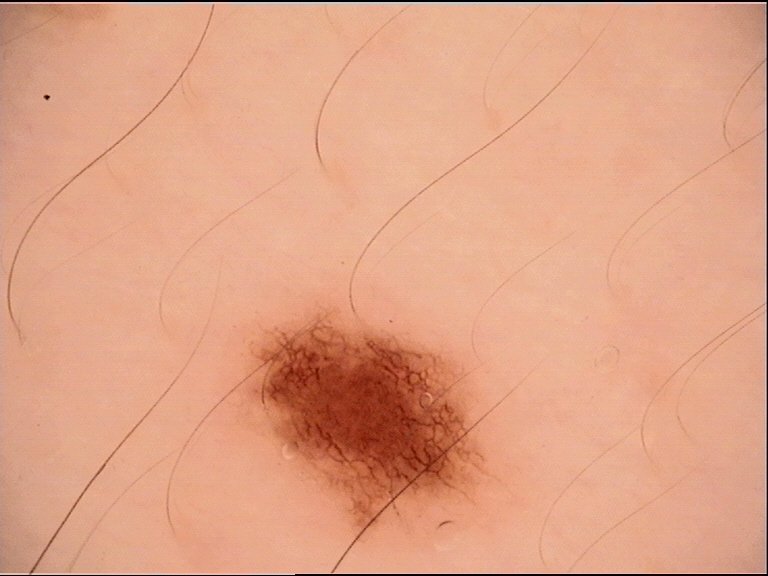Findings:
– image — dermatoscopy
– diagnosis — dysplastic junctional nevus (expert consensus)